A dermoscopic photograph of a skin lesion.
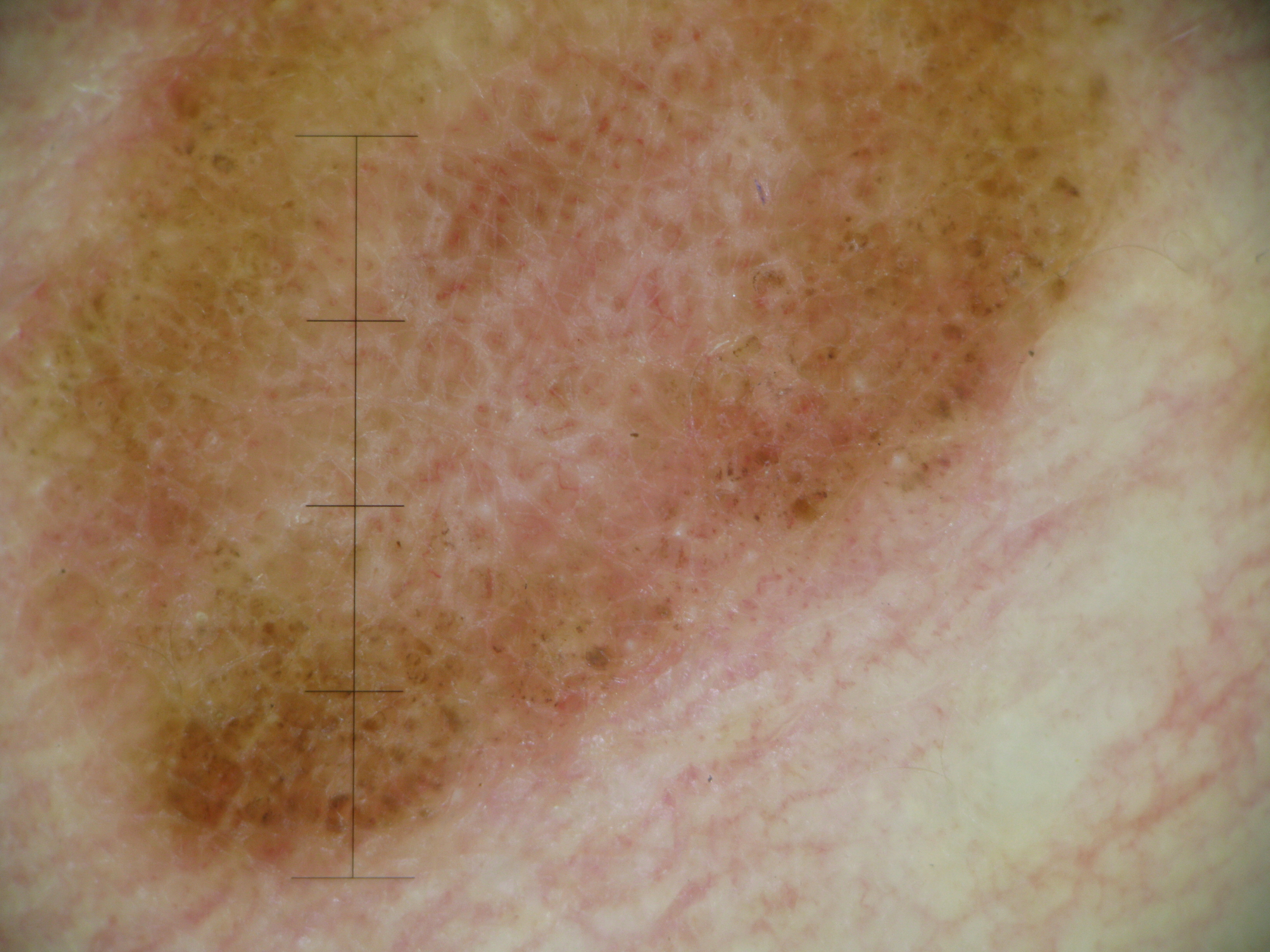Consistent with a banal lesion — a compound nevus.